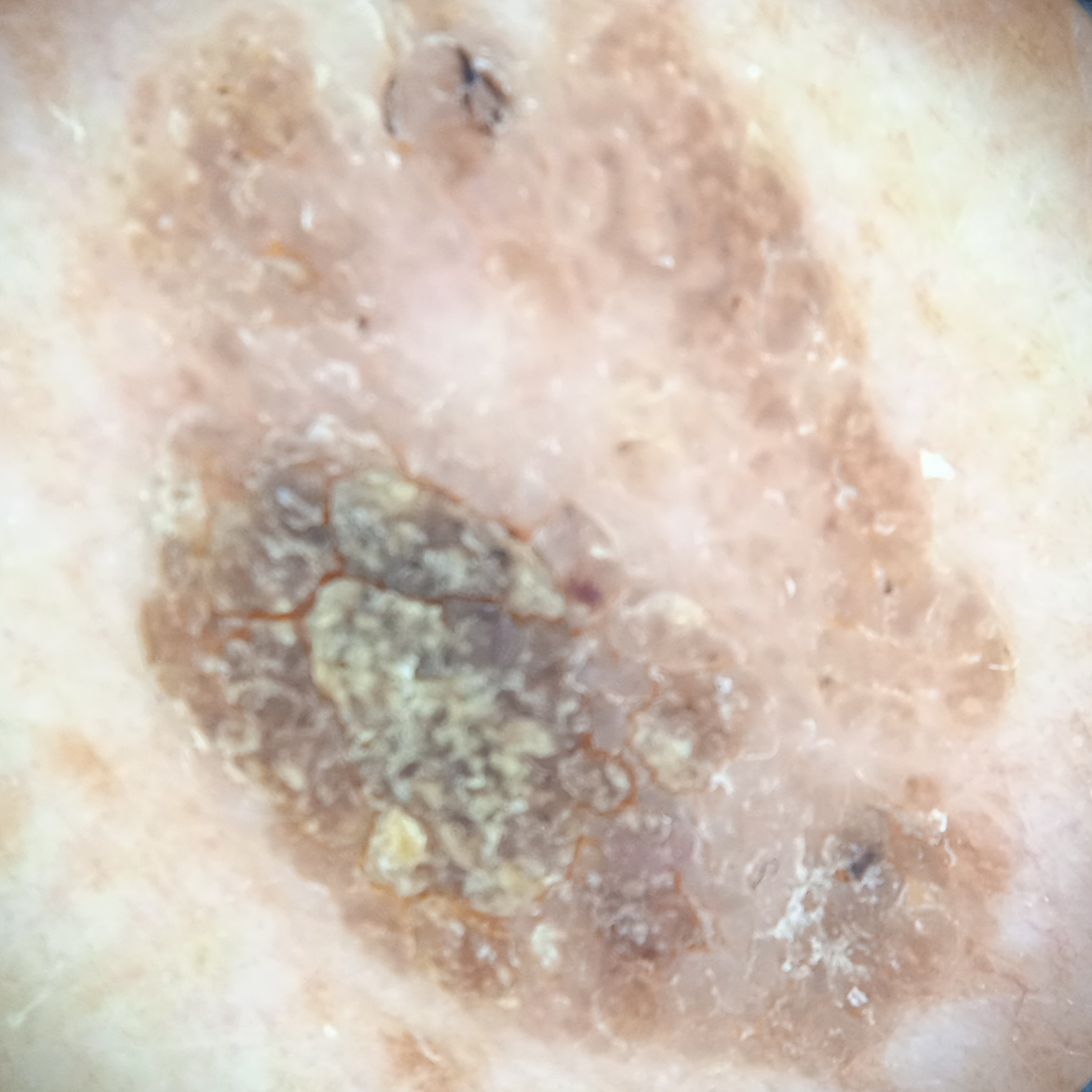| feature | finding |
|---|---|
| diagnostic label | seborrheic keratosis (dermatologist consensus) |